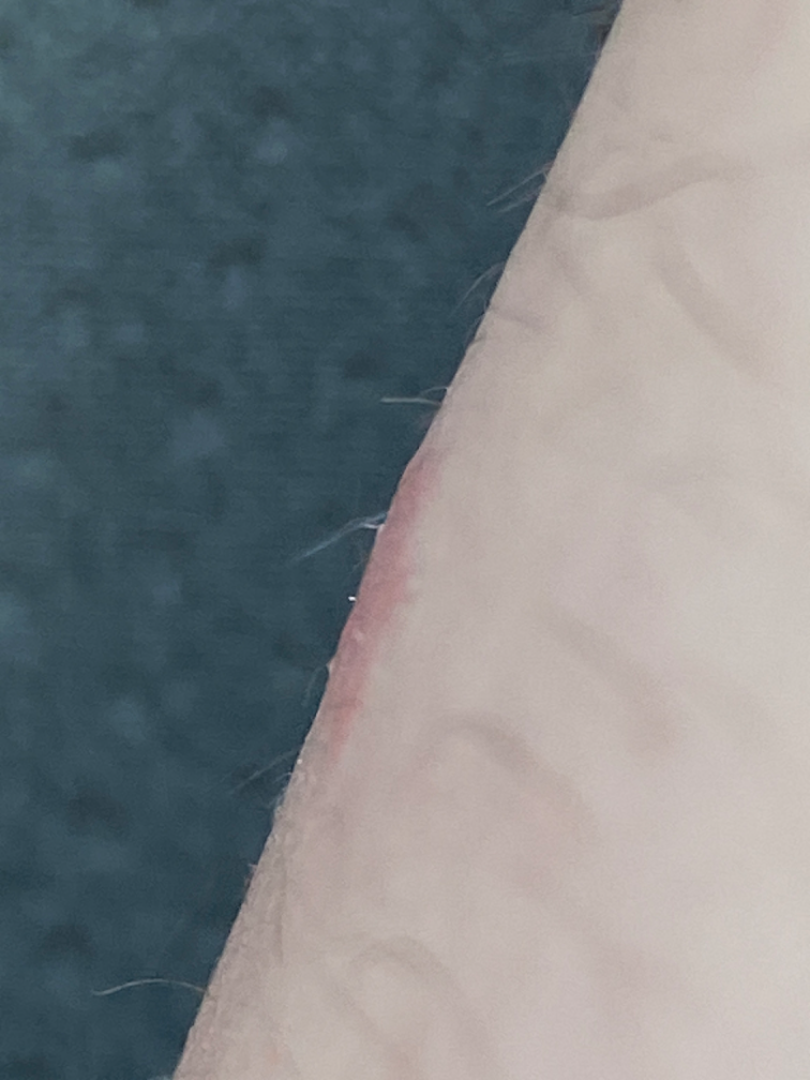Findings:
- assessment — ungradable on photographic review
- view — at an angle
- body site — leg